An image taken at an angle · the affected area is the arm and leg: 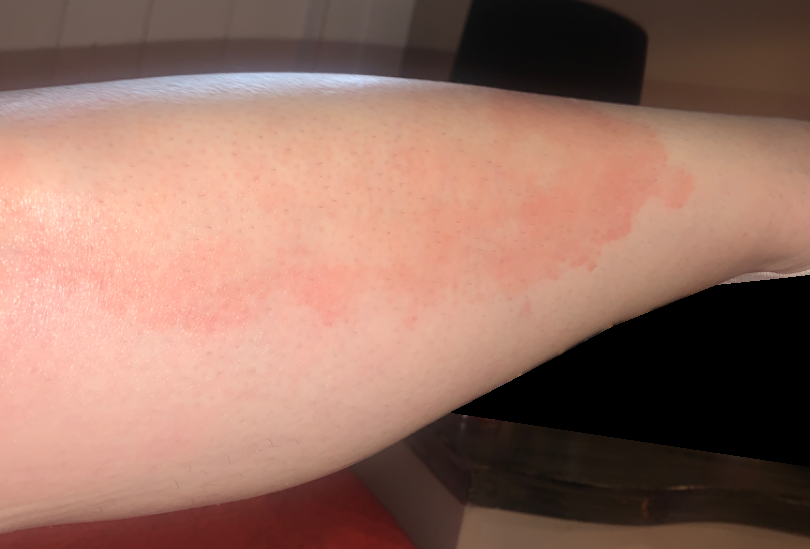| key | value |
|---|---|
| described texture | rough or flaky |
| onset | more than one year |
| impression | the differential is split between Psoriasis, Acute and chronic dermatitis and Necrobiosis lipoidica |